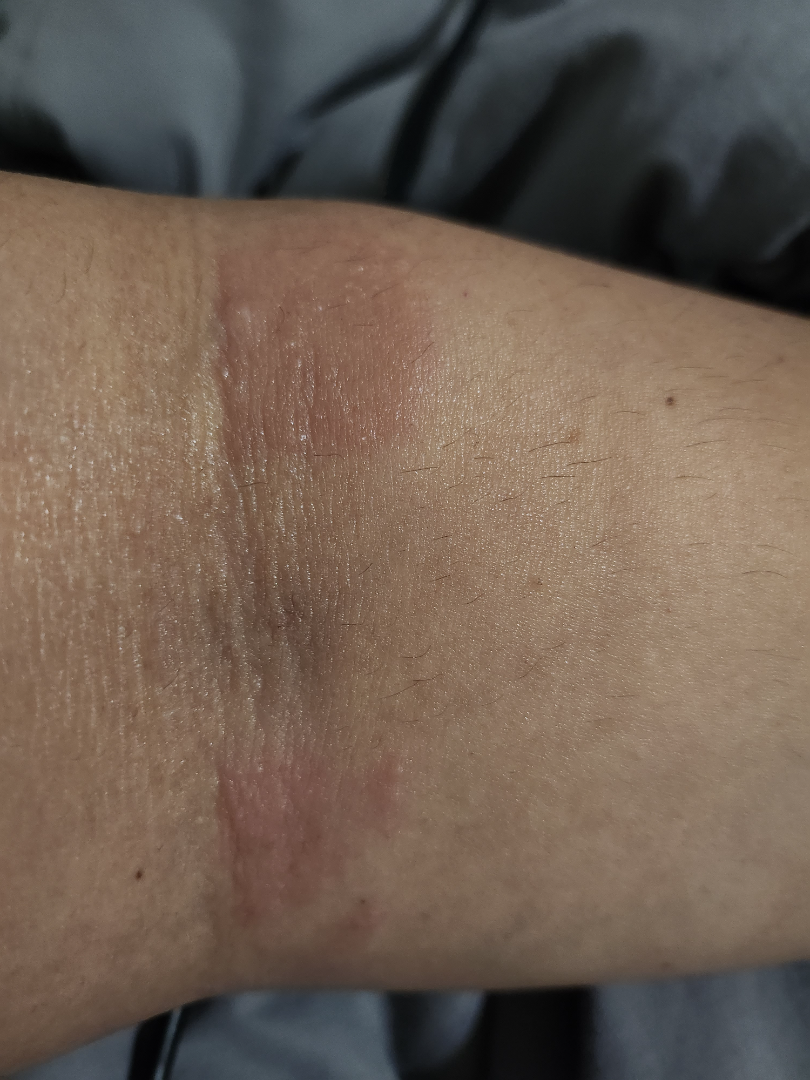The arm is involved. The photograph is a close-up of the affected area. On teledermatology review: in keeping with Eczema.